Present for one to four weeks. Located on the top or side of the foot, leg, arm, palm, back of the hand and sole of the foot. The lesion is associated with darkening, itching and bothersome appearance. The contributor notes associated chills. Skin tone: lay graders estimated Monk skin tone scale 4 or 6. This image was taken at a distance — 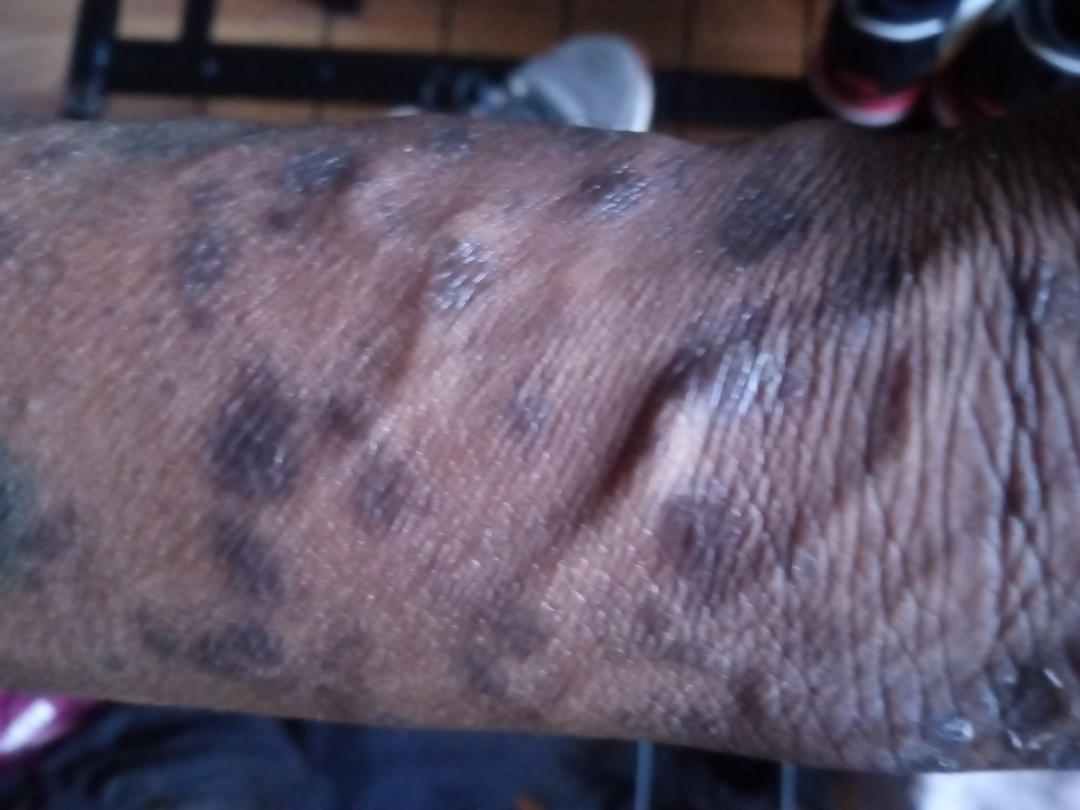<dermatology_case>
<differential>
  <tied_lead>Cutaneous T Cell Lymphoma, Kaposi's sarcoma of skin, Lichen planus/lichenoid eruption</tied_lead>
</differential>
</dermatology_case>